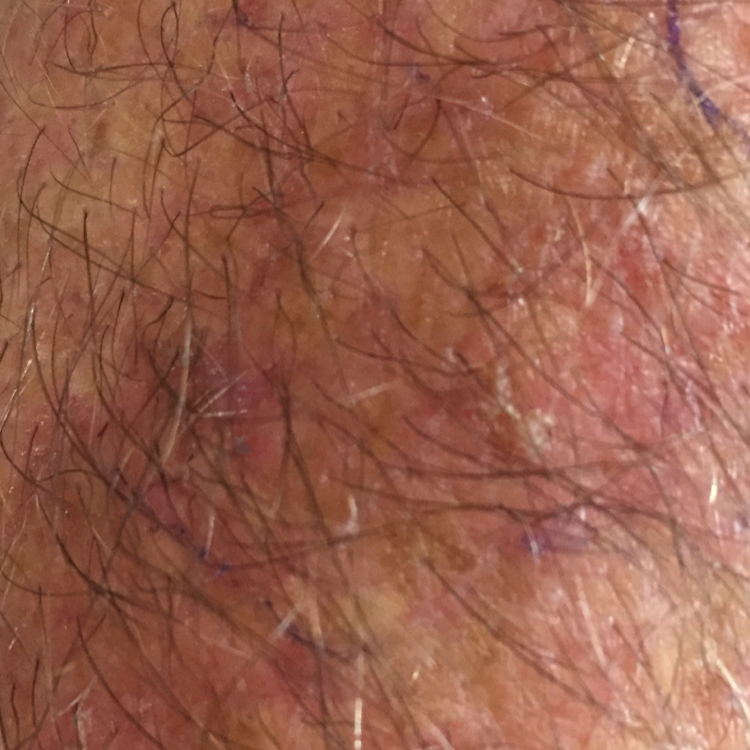diagnostic label: actinic keratosis (clinical consensus).